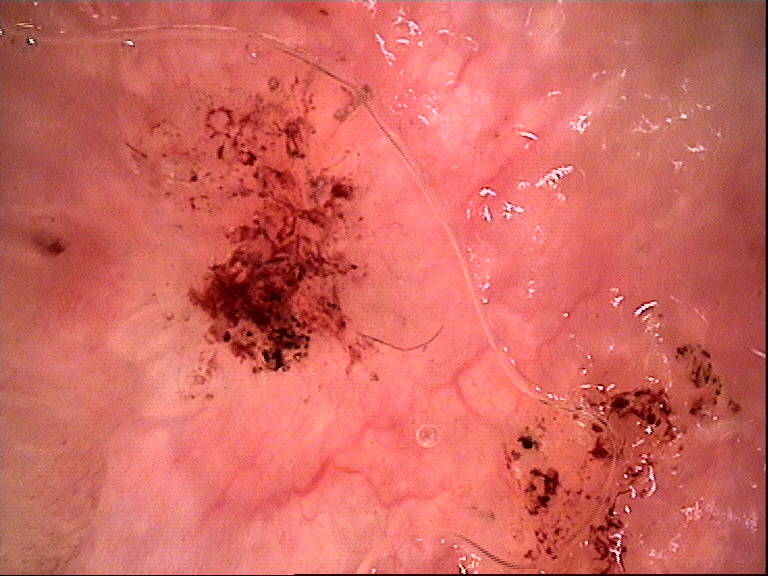Summary:
A dermoscopy image of a single skin lesion.
Conclusion:
Histopathologically confirmed as a malignancy — a basal cell carcinoma.